A dermoscopic photograph of a skin lesion.
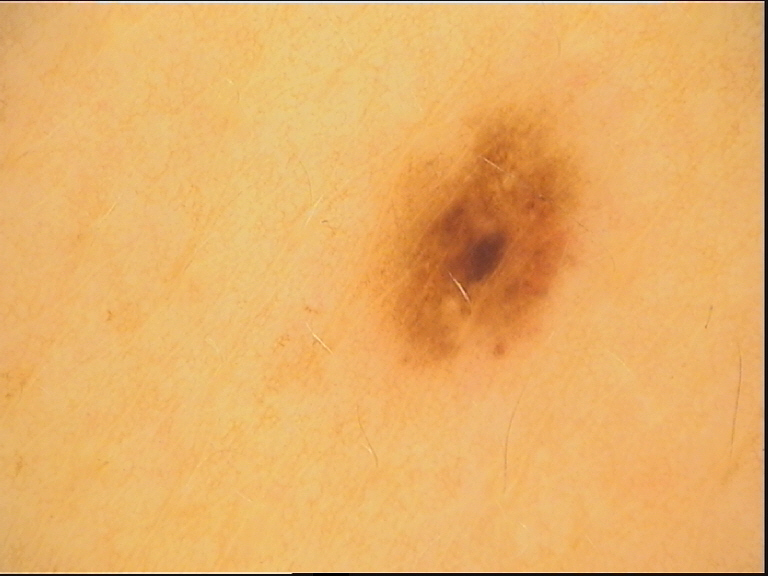diagnostic label=dysplastic junctional nevus (expert consensus).